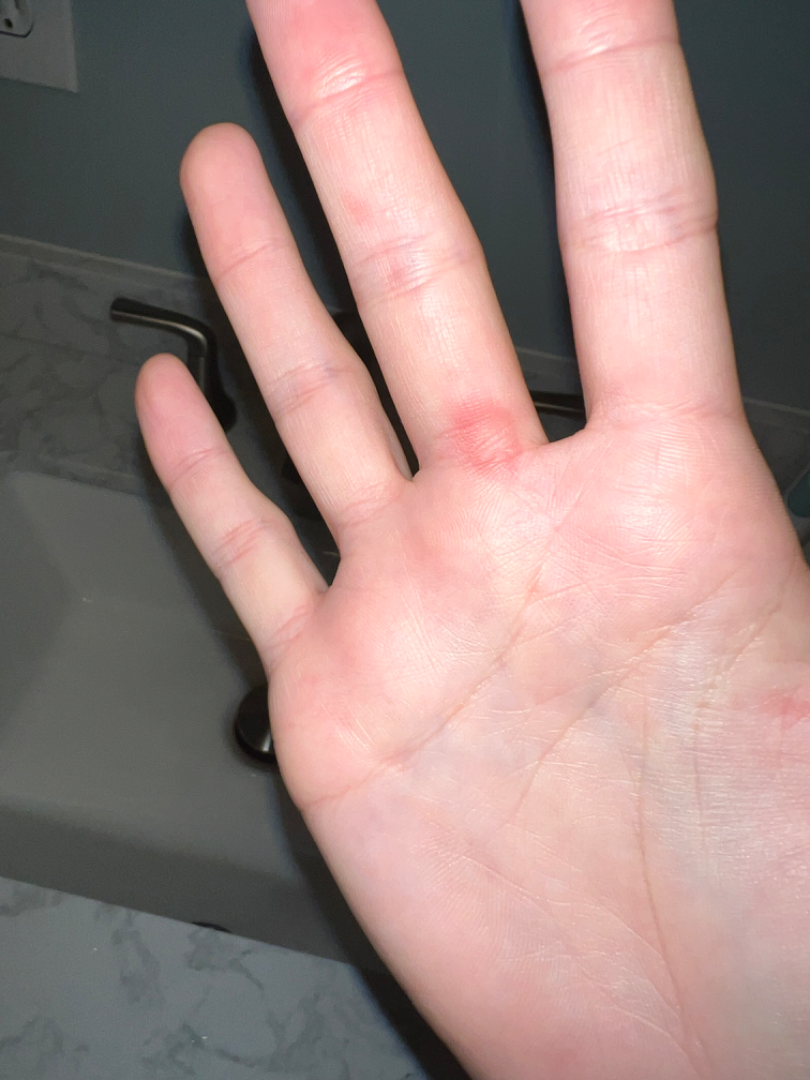Q: What is the affected area?
A: palm
Q: Age and sex?
A: female, age 18–29
Q: Texture?
A: raised or bumpy
Q: What is the framing?
A: at a distance
Q: What symptoms does the patient report?
A: none reported
Q: When did this start?
A: less than one week
Q: What is the dermatologist's impression?
A: the differential is split between Viral Exanthem, Erythema multiforme and Drug Rash